A dermoscopic image of a skin lesion:
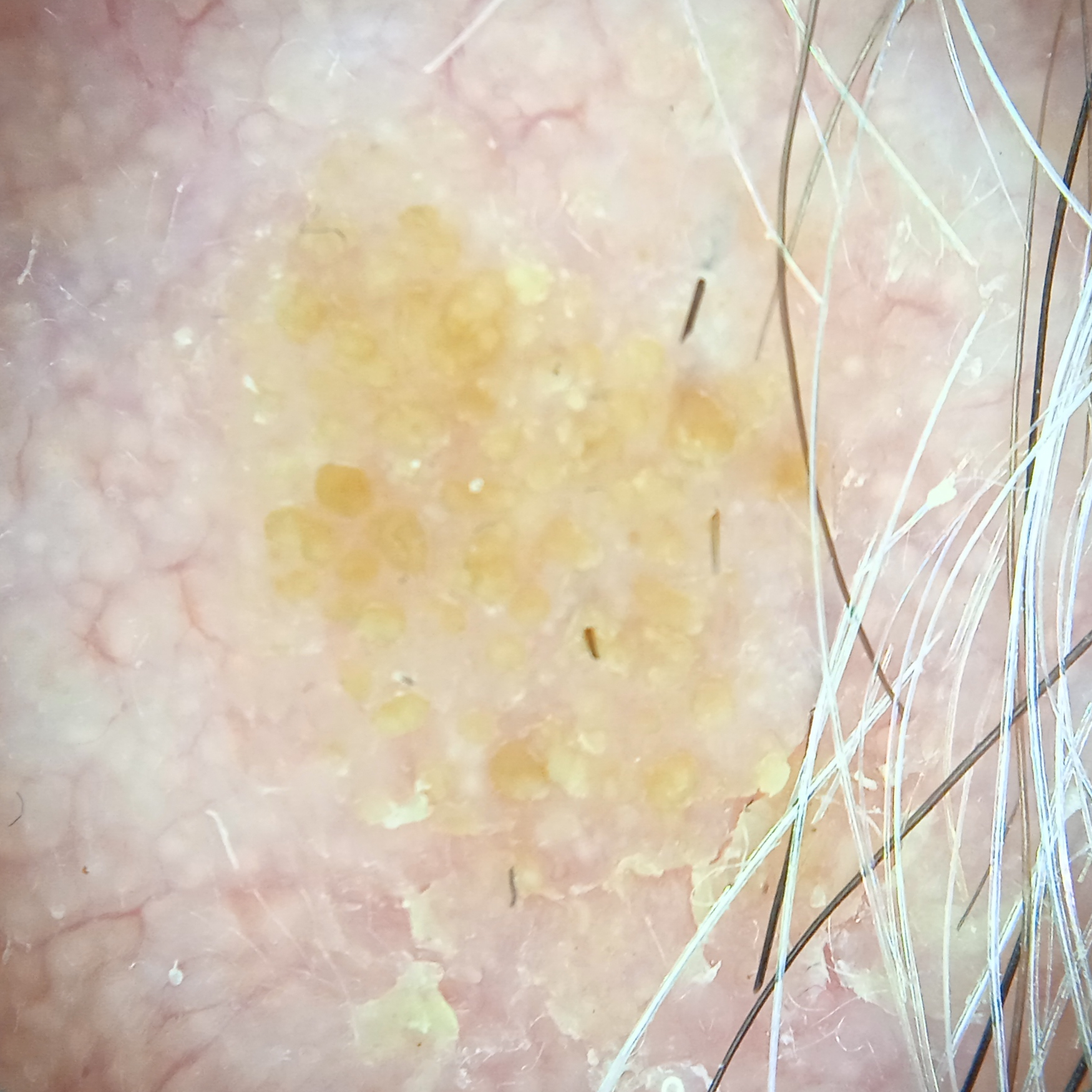The lesion is on the face.
The lesion measures approximately 8.8 mm.
The consensus diagnosis for this lesion was a seborrheic keratosis.